A dermoscopy image of a skin lesion · the patient reports no immunosuppression and no personal history of cancer · imaged for a research study, with no referral diagnosis recorded:
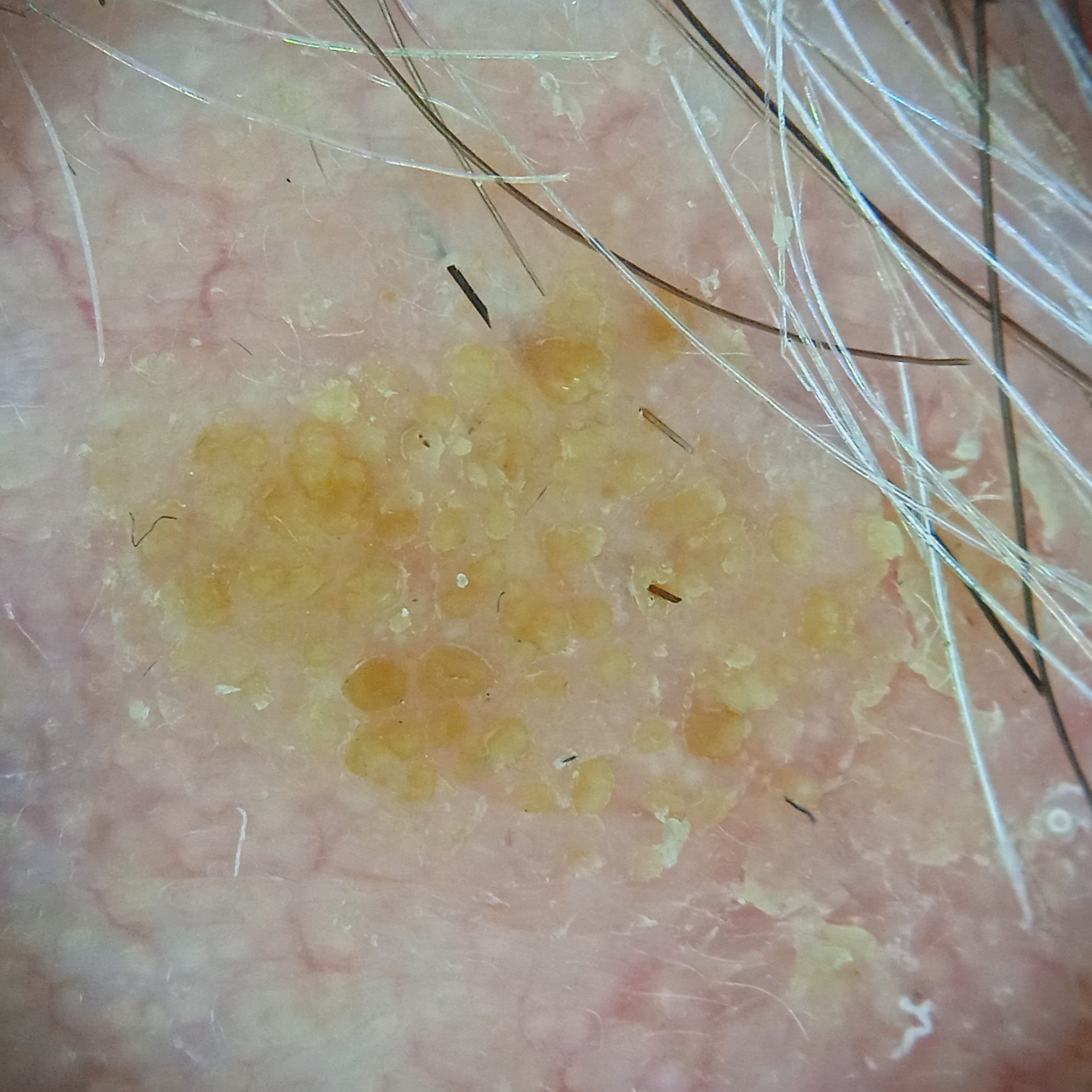Summary: The lesion is on the face. The lesion measures approximately 8.8 mm. Conclusion: The lesion was assessed as a seborrheic keratosis.